Close-up view.
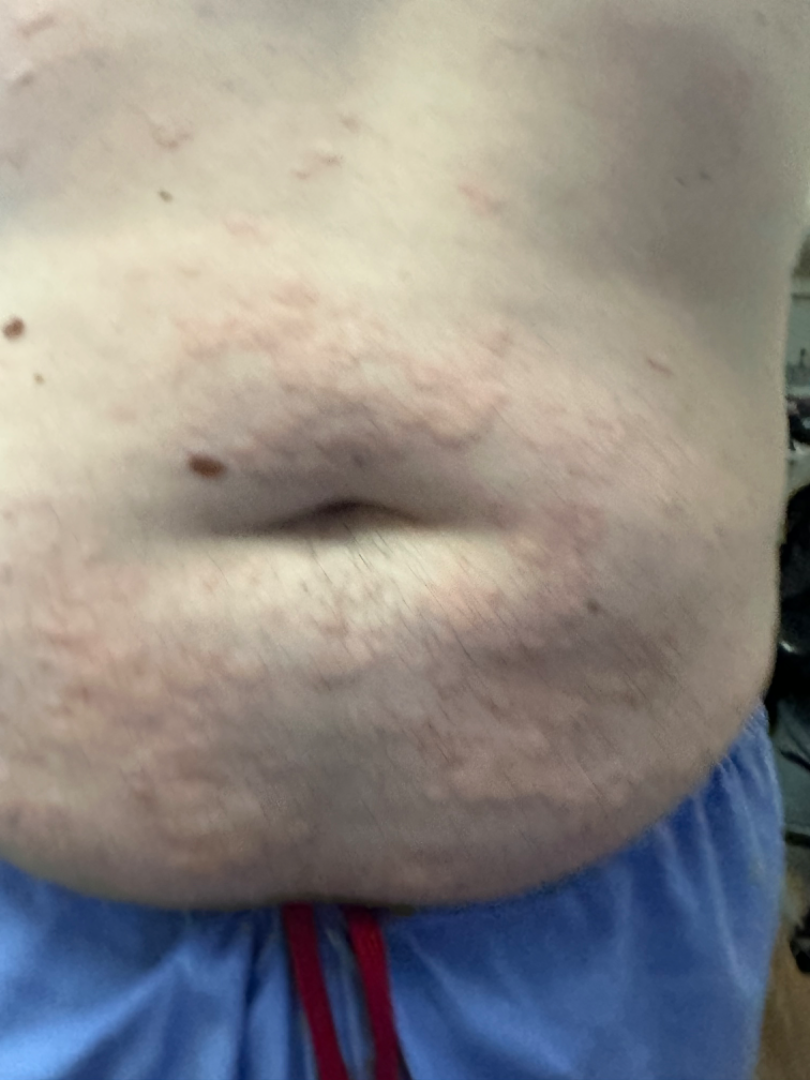Q: Could the case be diagnosed?
A: unable to determine